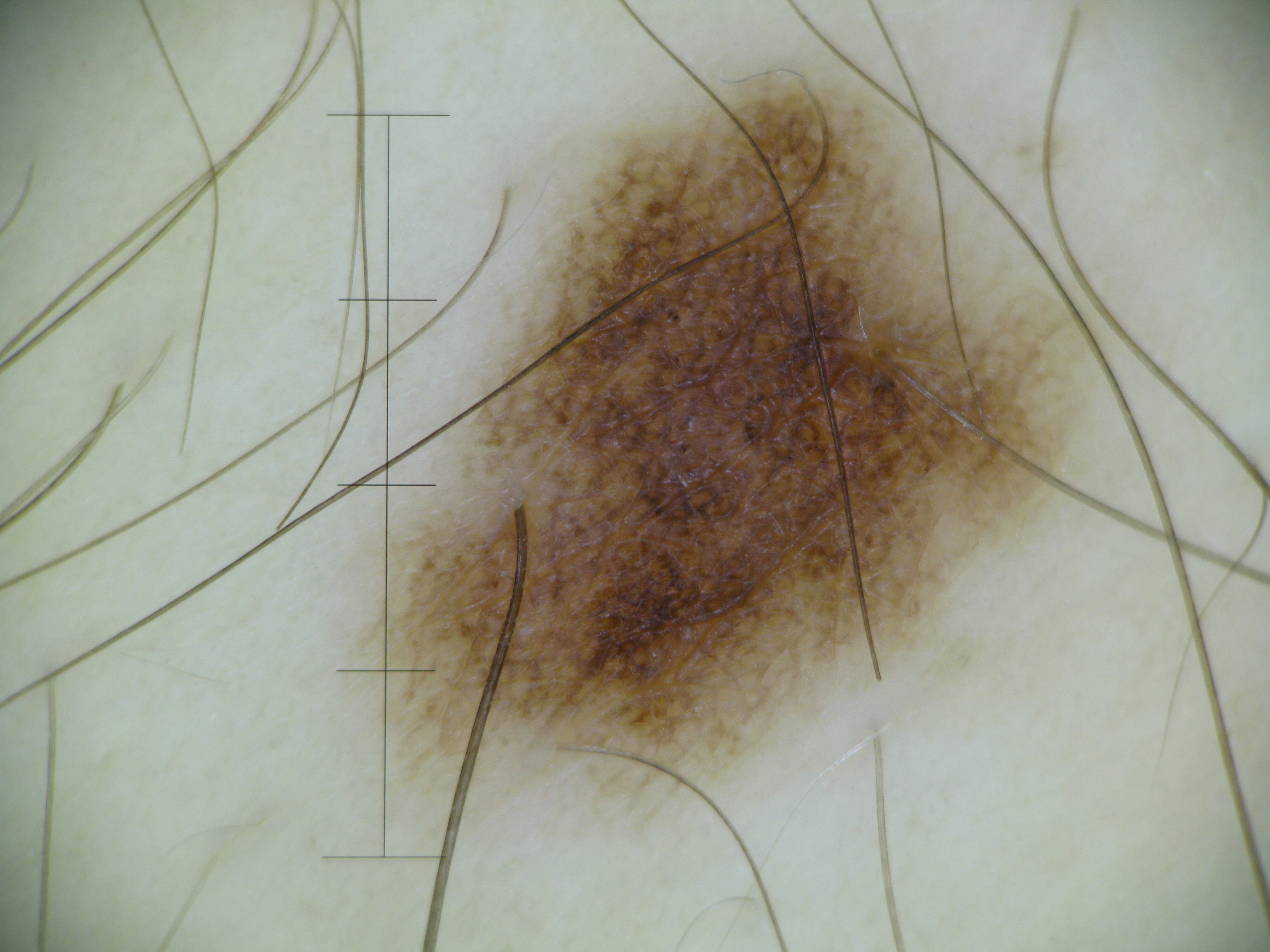image: dermatoscopy
diagnosis:
  name: dysplastic junctional nevus
  code: jd
  malignancy: benign
  super_class: melanocytic
  confirmation: expert consensus